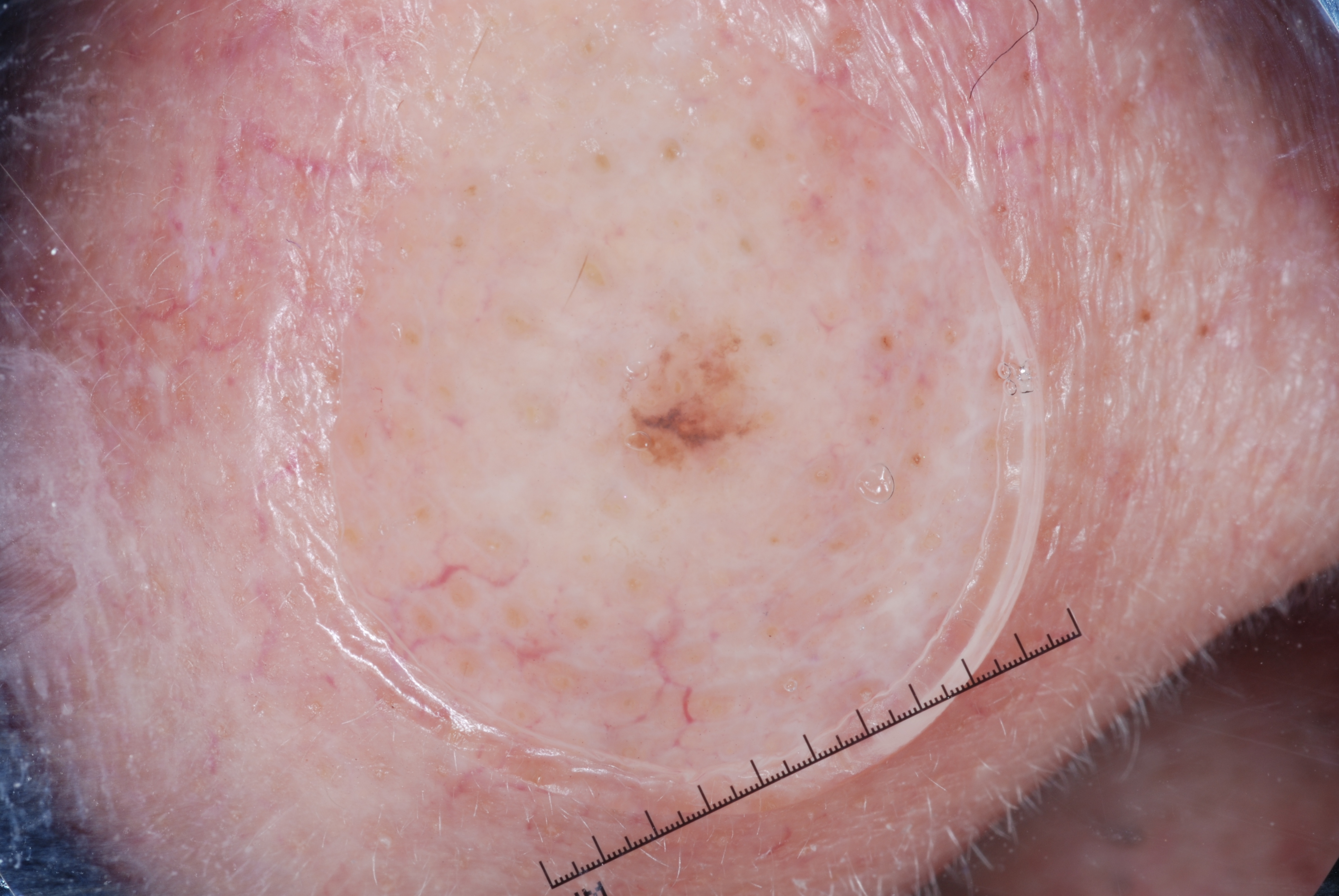  patient:
    sex: male
    age_approx: 80
  image:
    modality: dermoscopy
  dermoscopic_features:
    present: []
    absent:
      - streaks
      - negative network
      - milia-like cysts
      - pigment network
  lesion_location: spans the dermoscopic field
  diagnosis:
    name: melanocytic nevus
    malignancy: benign
    lineage: melanocytic
    provenance: clinical